Self-categorized by the patient as a rash. Present for one to four weeks. The photograph is a close-up of the affected area. The lesion is described as raised or bumpy, fluid-filled and flat. The patient reported no systemic symptoms. Located on the leg. The patient is female.
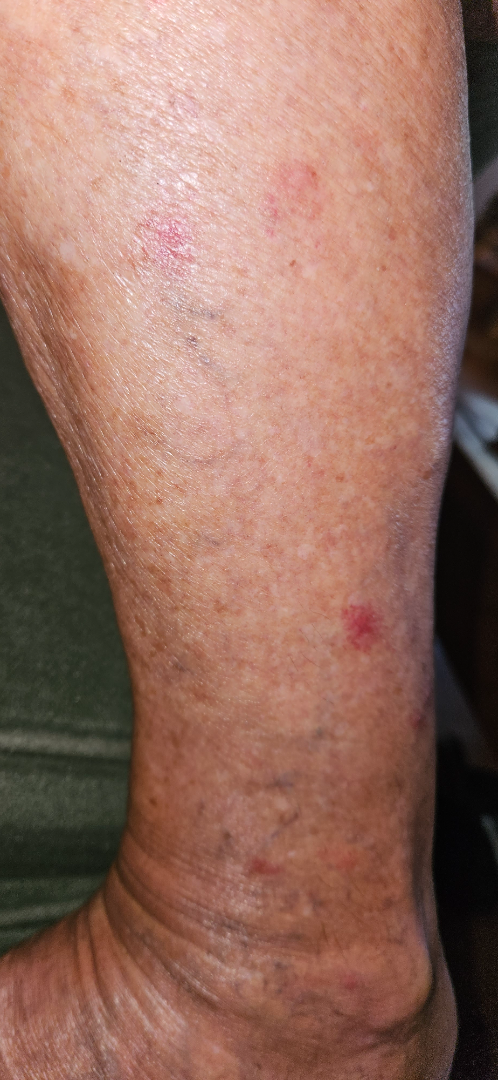| field | value |
|---|---|
| diagnostic considerations | the differential, in no particular order, includes Insect Bite, Eczema and Leukocytoclastic Vasculitis |